A skin lesion imaged with a dermatoscope: 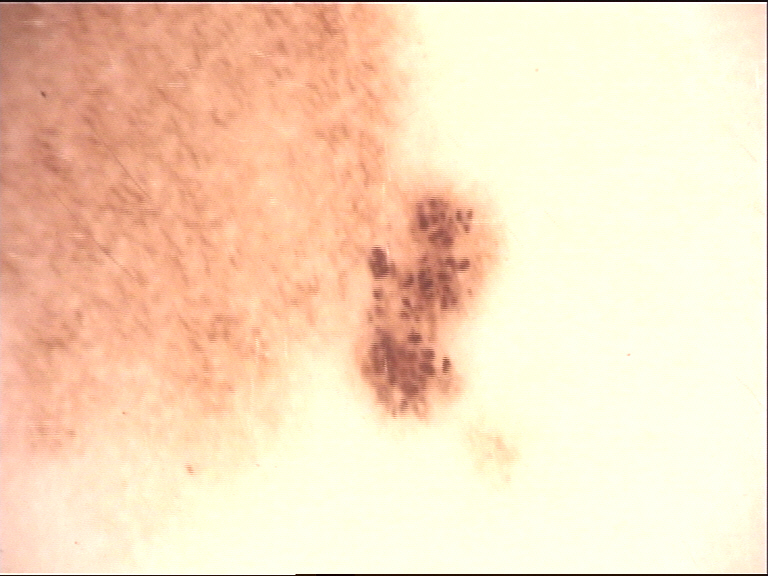Impression:
The diagnostic label was a banal lesion — a congenital junctional nevus.